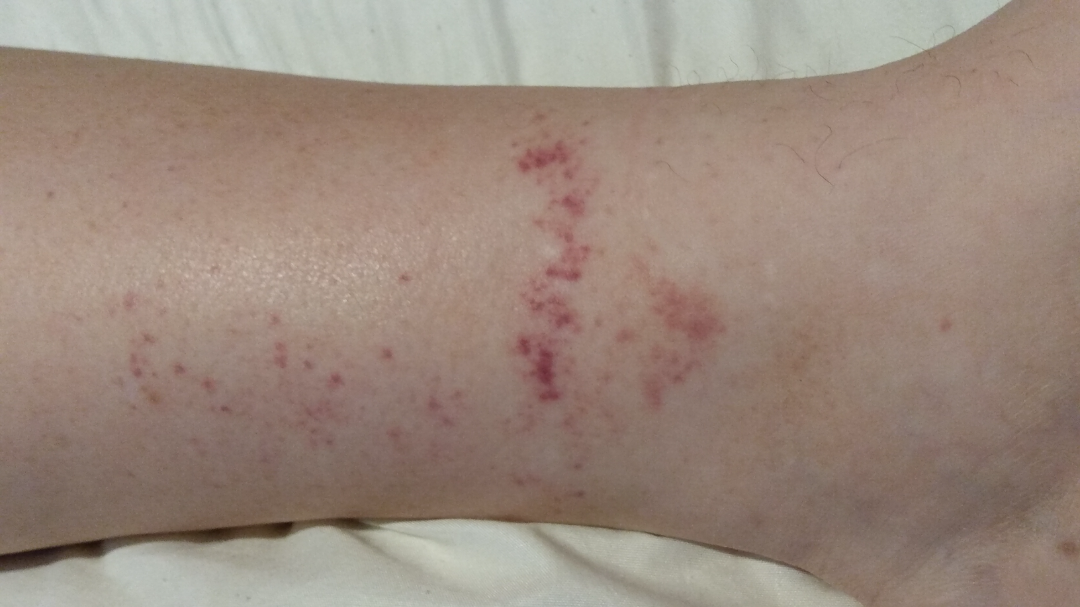<summary>
<patient>female, age 40–49</patient>
<body_site>leg</body_site>
<systemic_symptoms>none reported</systemic_symptoms>
<shot_type>at an angle</shot_type>
<symptoms>enlargement, bothersome appearance, darkening</symptoms>
<duration>less than one week</duration>
<texture>flat</texture>
<differential>
  <tied_lead>Pigmented purpuric eruption, Vasculitis of the skin</tied_lead>
</differential>
</summary>